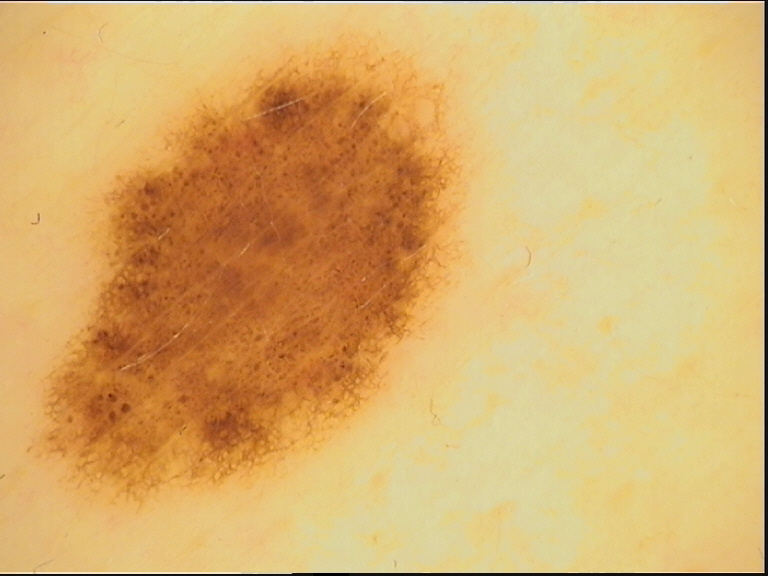Diagnosed as a dysplastic junctional nevus.